This image was taken at an angle; the patient is 30–39, female; reported lesion symptoms include enlargement and itching; self-categorized by the patient as a rash.
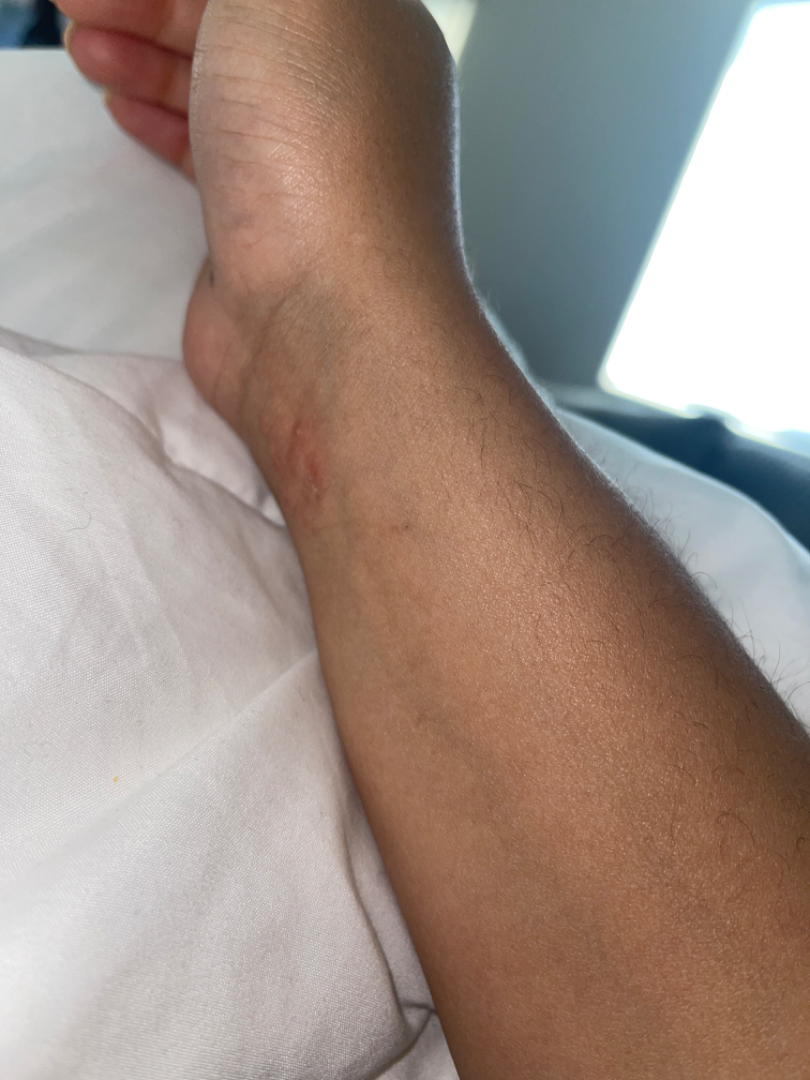Q: What is the dermatologist's impression?
A: reviewed remotely by one dermatologist: the leading impression is Allergic Contact Dermatitis; possibly Impetigo; also consider Herpes Zoster